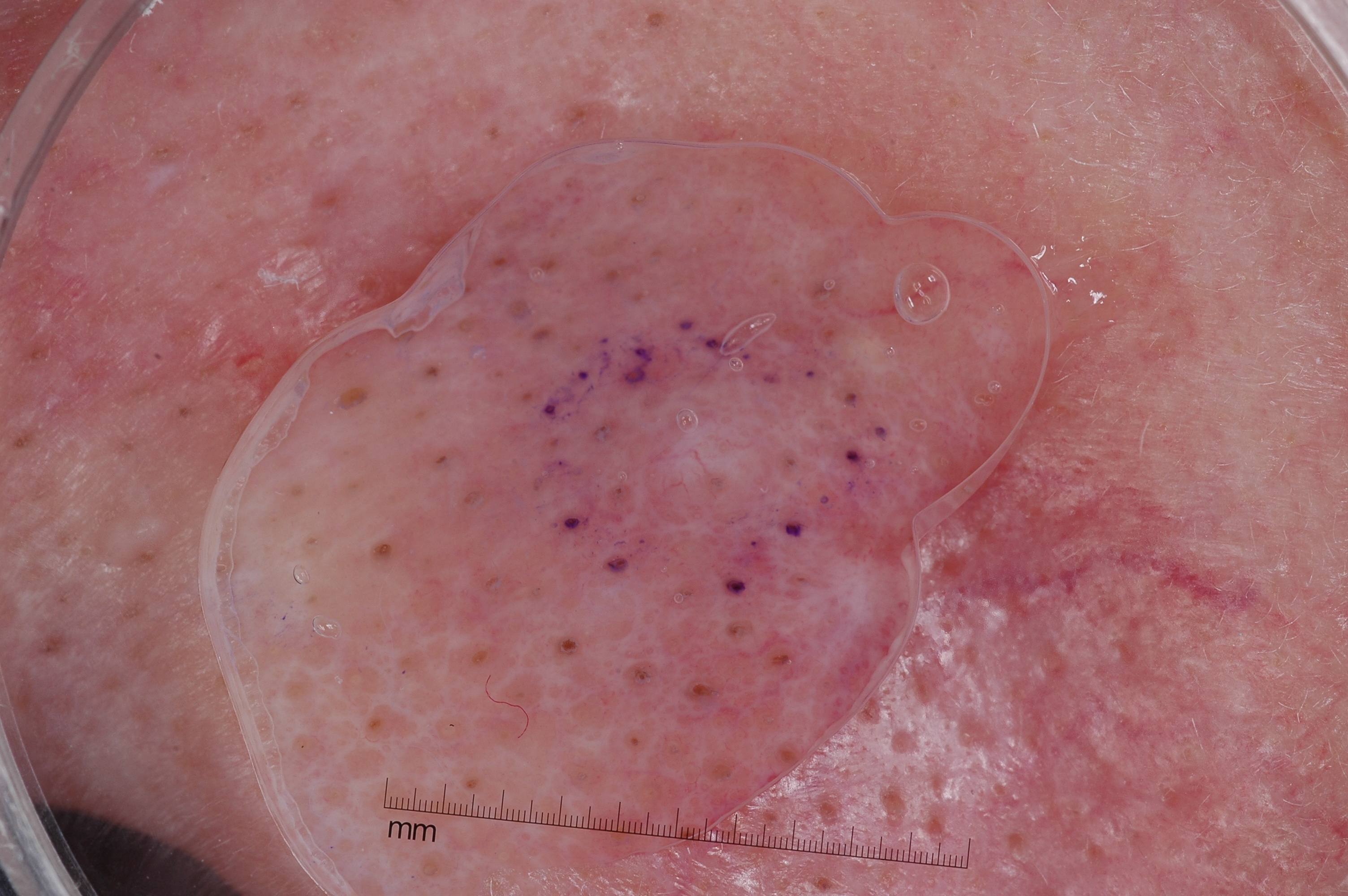<case>
  <patient>
    <sex>female</sex>
    <age_approx>65</age_approx>
  </patient>
  <image>
    <modality>dermoscopy</modality>
  </image>
  <dermoscopic_features>
    <present/>
    <absent>negative network, milia-like cysts, pigment network, streaks</absent>
  </dermoscopic_features>
  <lesion_location>
    <bbox_xyxy>557, 367, 794, 559</bbox_xyxy>
  </lesion_location>
  <lesion_extent>
    <approx_field_fraction_pct>3</approx_field_fraction_pct>
  </lesion_extent>
  <diagnosis>
    <name>melanocytic nevus</name>
    <malignancy>benign</malignancy>
    <lineage>melanocytic</lineage>
    <provenance>clinical</provenance>
  </diagnosis>
</case>